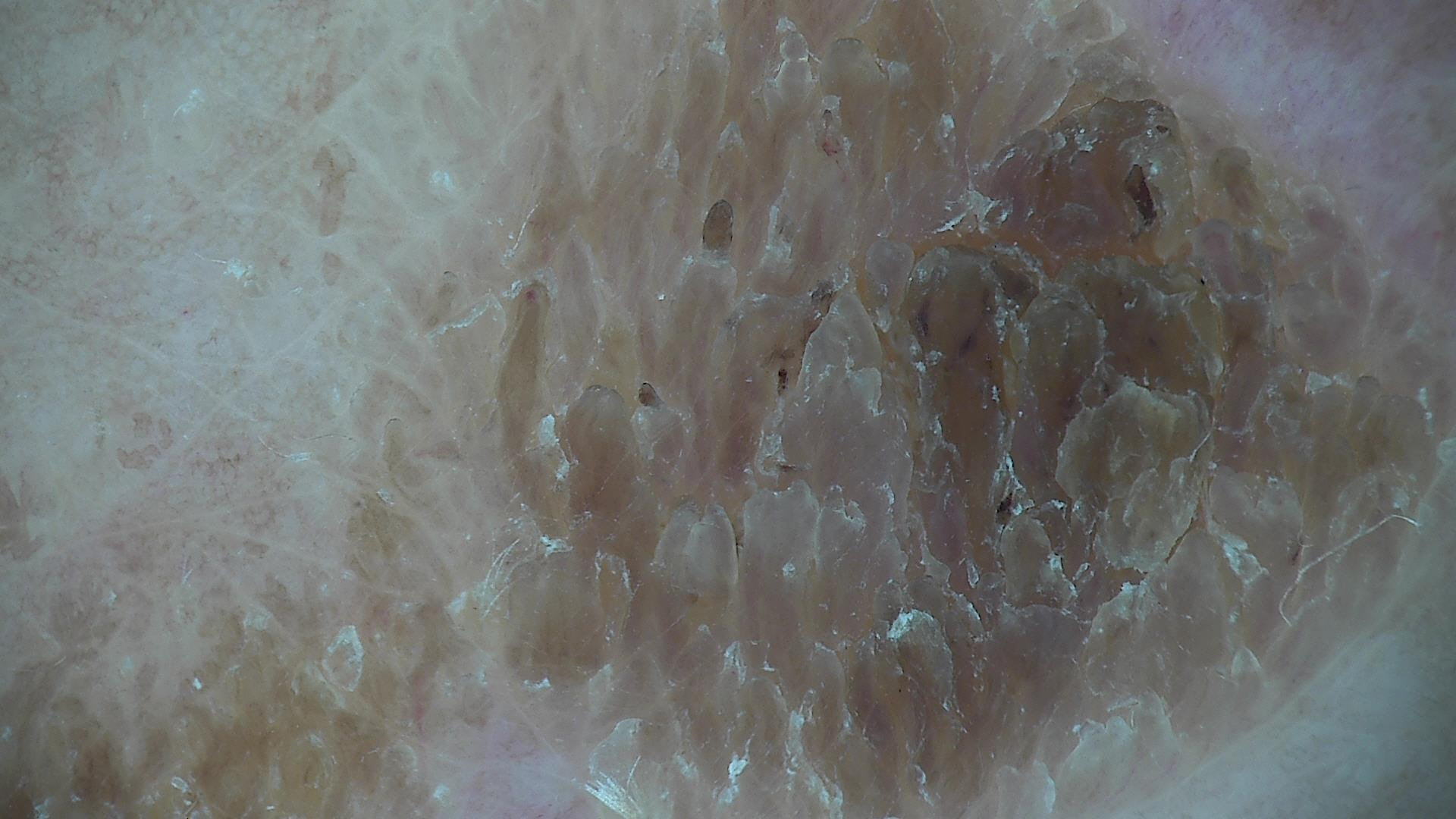Case:
– imaging — dermatoscopy
– assessment — seborrheic keratosis (expert consensus)